A dermatoscopic image of a skin lesion · the patient is a female in their 60s.
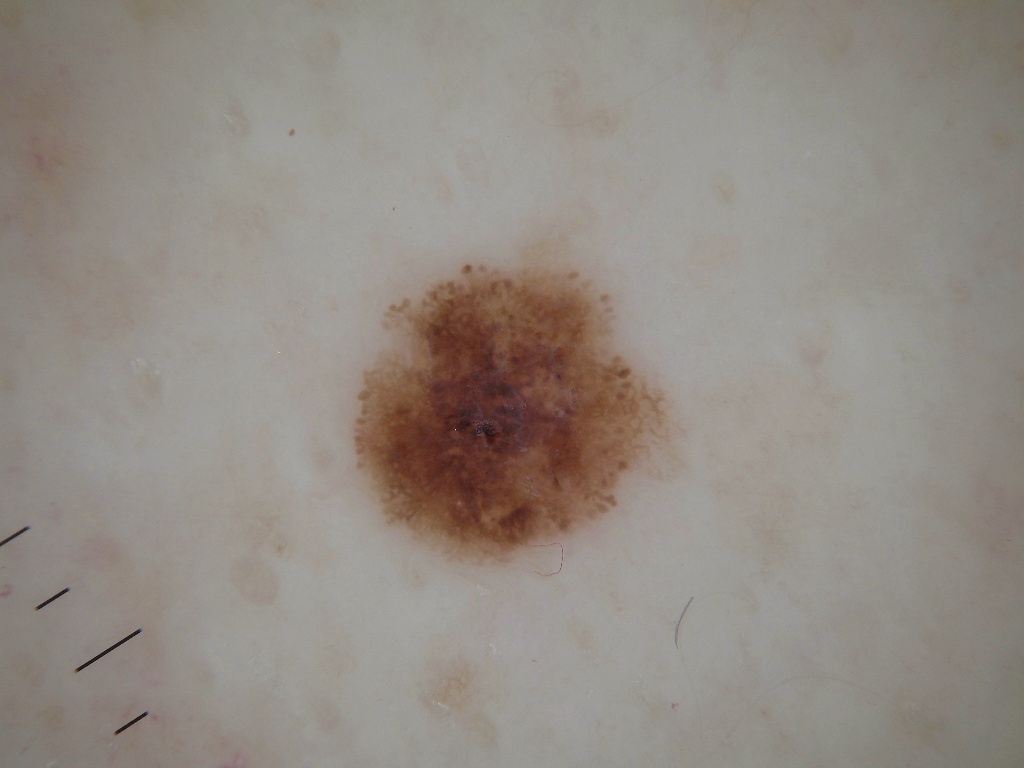lesion_location:
  bbox_xyxy:
    - 339
    - 222
    - 683
    - 576
dermoscopic_features:
  present:
    - pigment network
  absent:
    - streaks
    - negative network
    - milia-like cysts
    - globules
diagnosis:
  name: melanocytic nevus
  malignancy: benign
  lineage: melanocytic
  provenance: clinical